A dermoscopic image of a skin lesion:
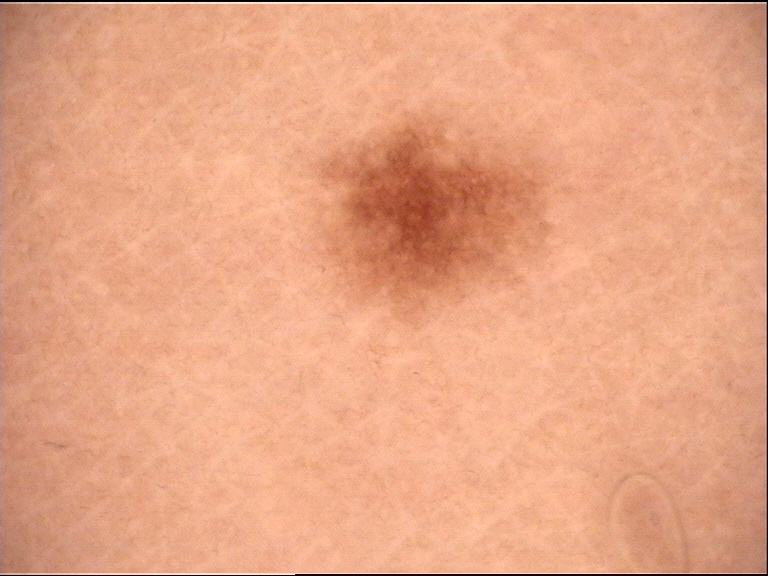{"lesion_type": {"main_class": "banal", "pattern": "junctional"}, "diagnosis": {"name": "junctional nevus", "code": "jb", "malignancy": "benign", "super_class": "melanocytic", "confirmation": "expert consensus"}}